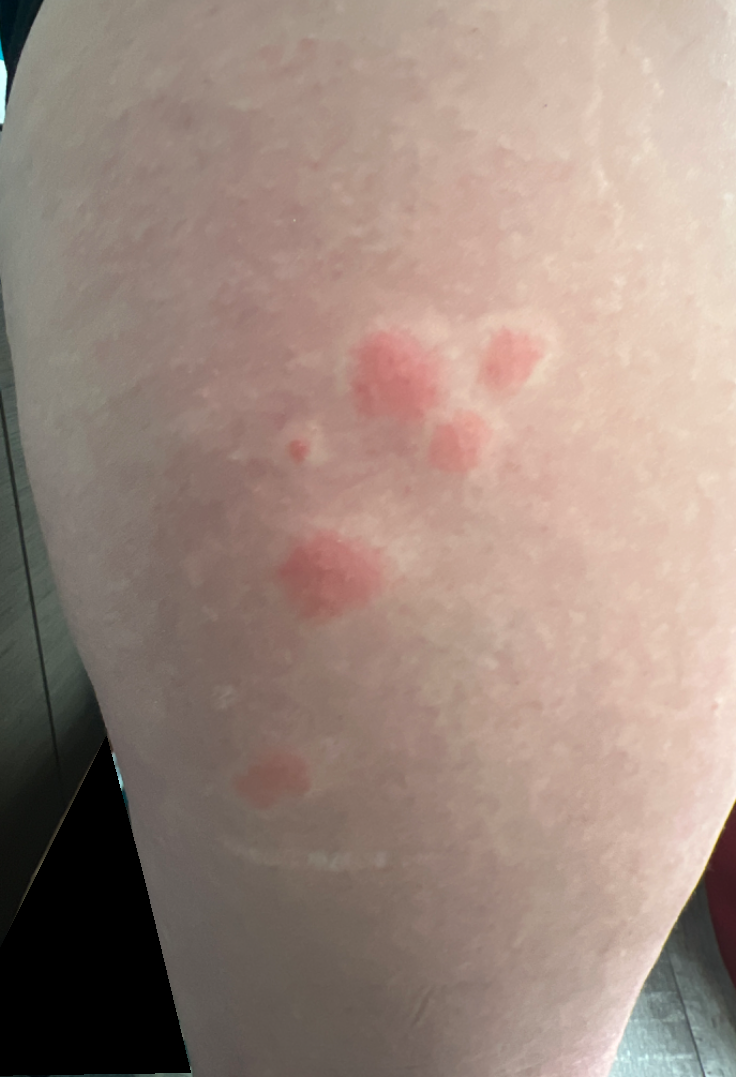Q: Fitzpatrick or Monk tone?
A: non-clinician graders estimated MST 1–2
Q: How was the photo taken?
A: close-up
Q: What is the differential diagnosis?
A: Insect Bite (considered); Eczema (considered)